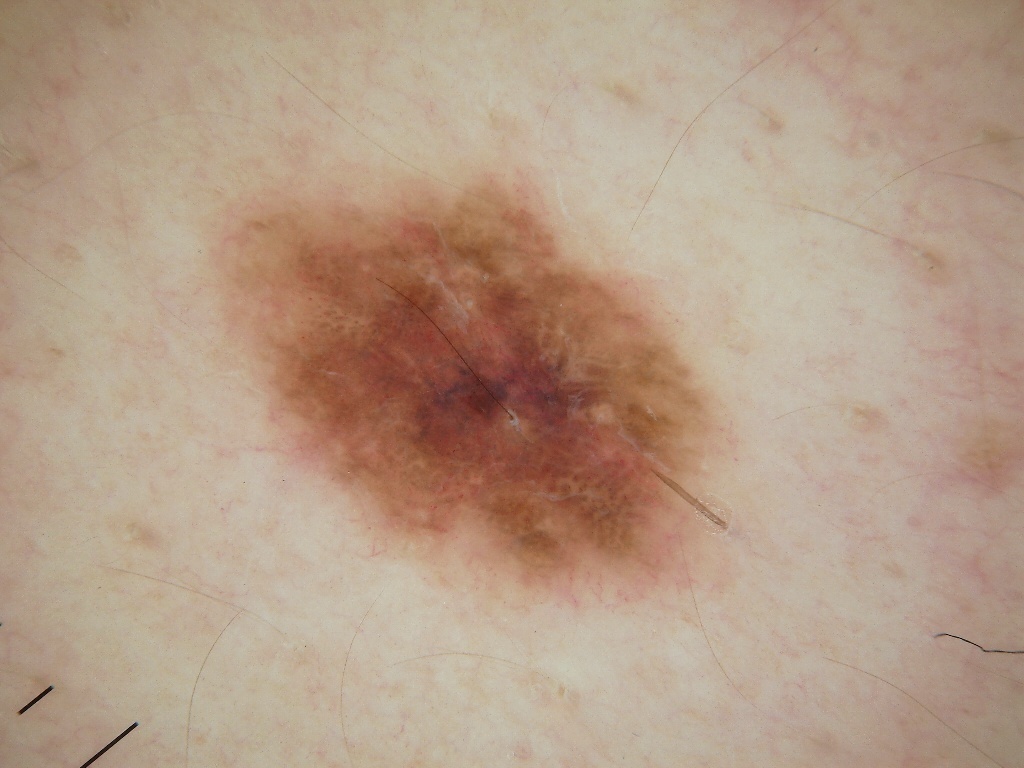A dermoscopy image of a single skin lesion. A male subject, aged 38 to 42. The lesion occupies roughly 18% of the field. The dermoscopic pattern shows negative network and globules, with no pigment network, milia-like cysts, or streaks. The lesion is located at x1=212, y1=173, x2=712, y2=596. On biopsy, the diagnosis was a melanoma, a malignant skin lesion.